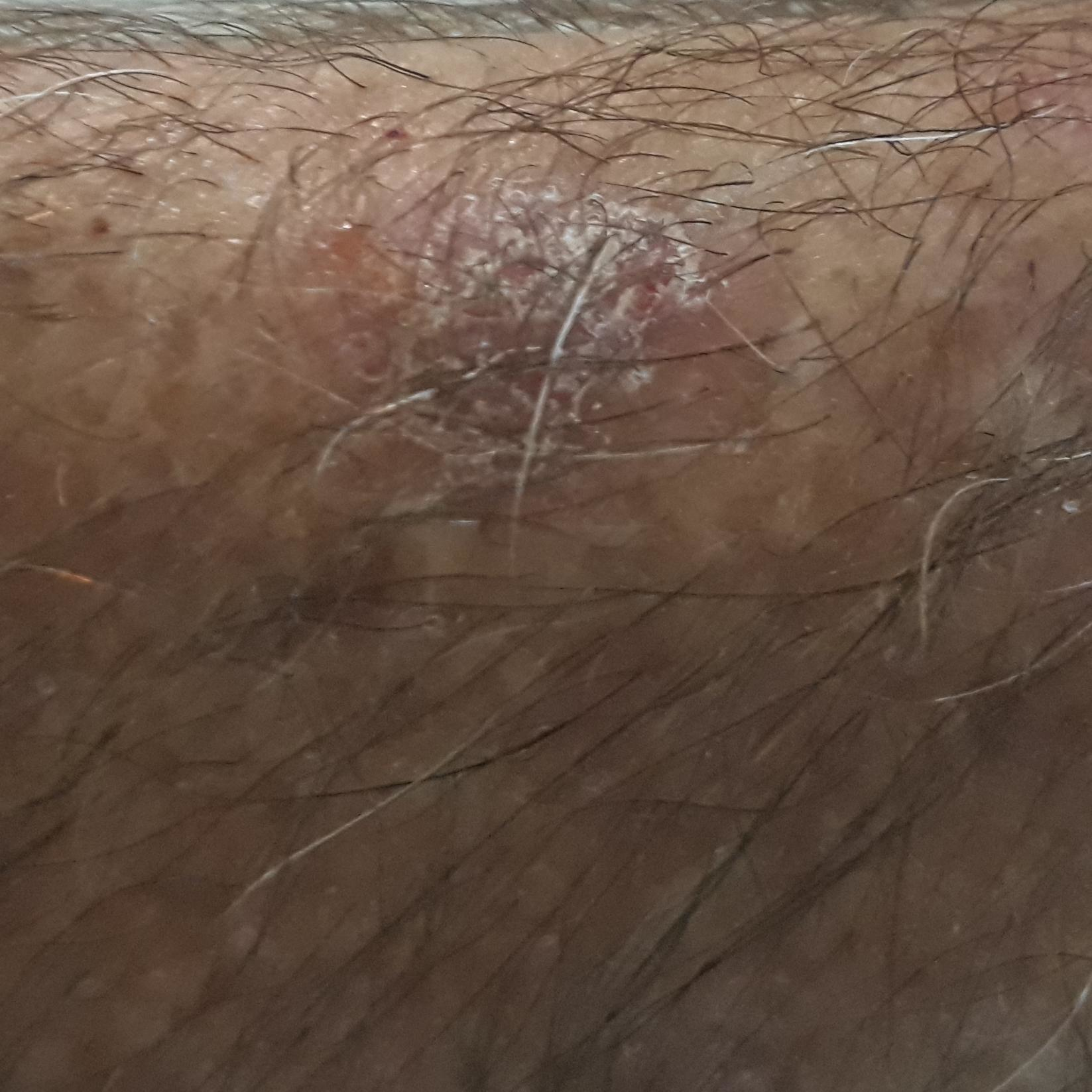| field | value |
|---|---|
| risk factors | prior malignancy (patient or family), pesticide exposure, alcohol use |
| skin phototype | III |
| image | clinical photograph |
| body site | a forearm |
| lesion size | 12 × 10 mm |
| patient-reported symptoms | growth, itching / no bleeding, no elevation |
| impression | actinic keratosis (clinical consensus) |